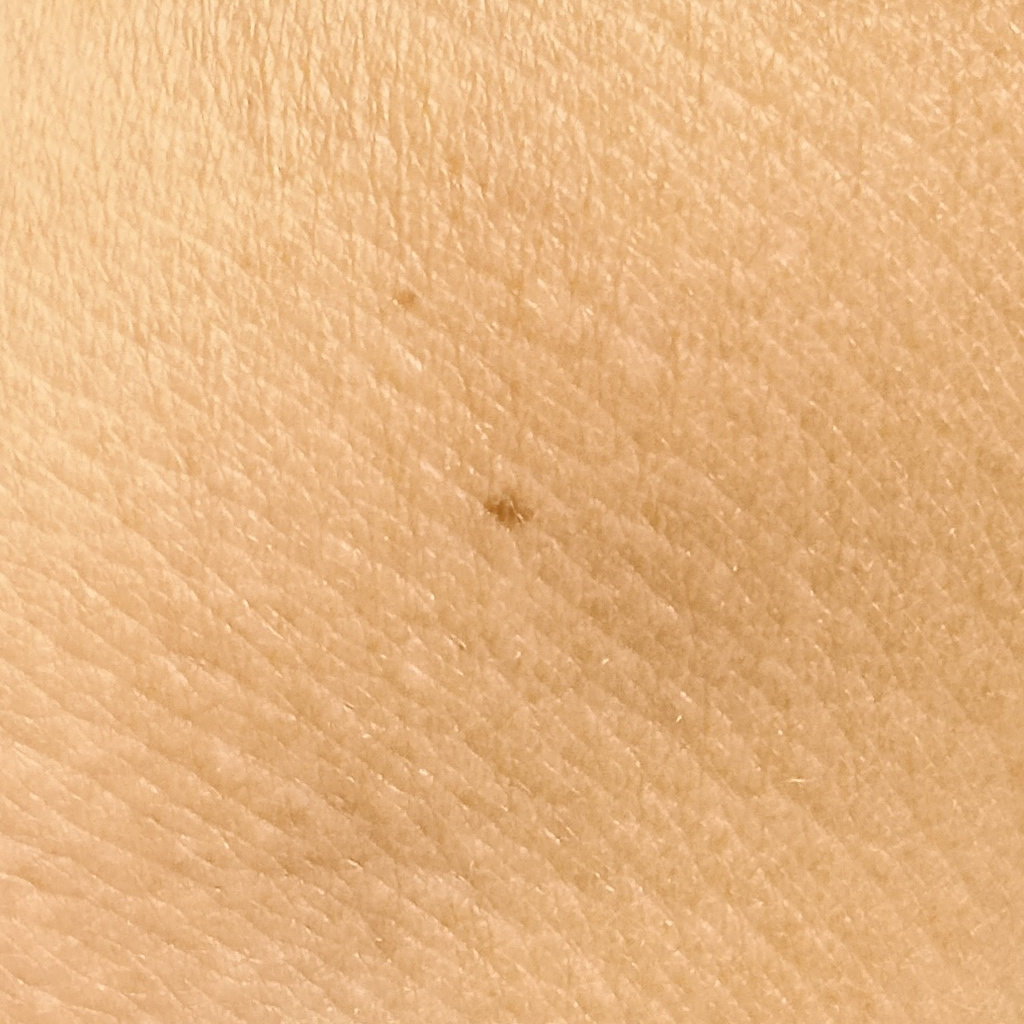<case>
  <diagnosis>
    <name>melanocytic nevus</name>
    <malignancy>benign</malignancy>
  </diagnosis>
</case>